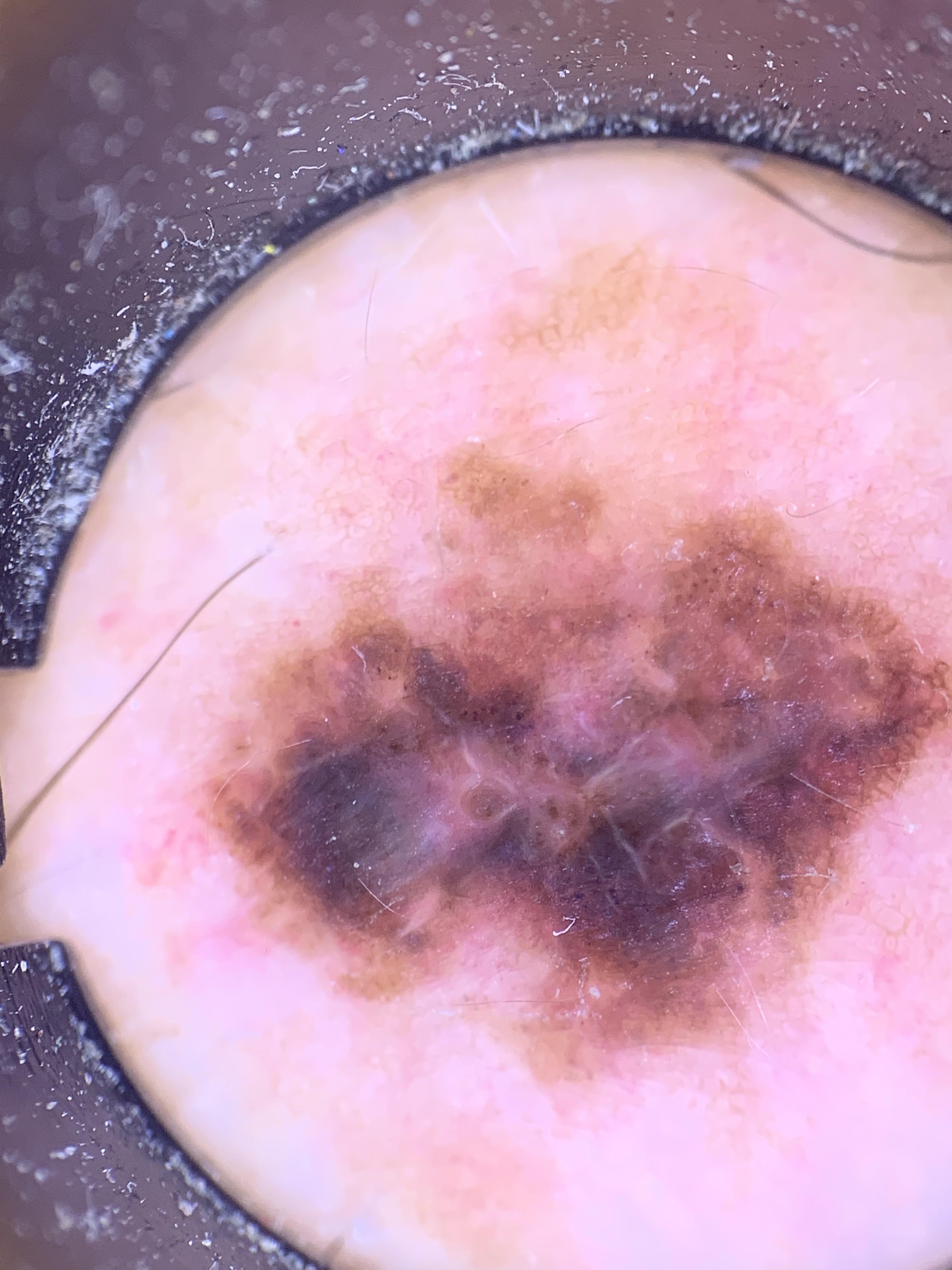* imaging: contact-polarized dermoscopy
* Fitzpatrick: III
* site: the trunk
* pathology: Nevus (biopsy-proven)